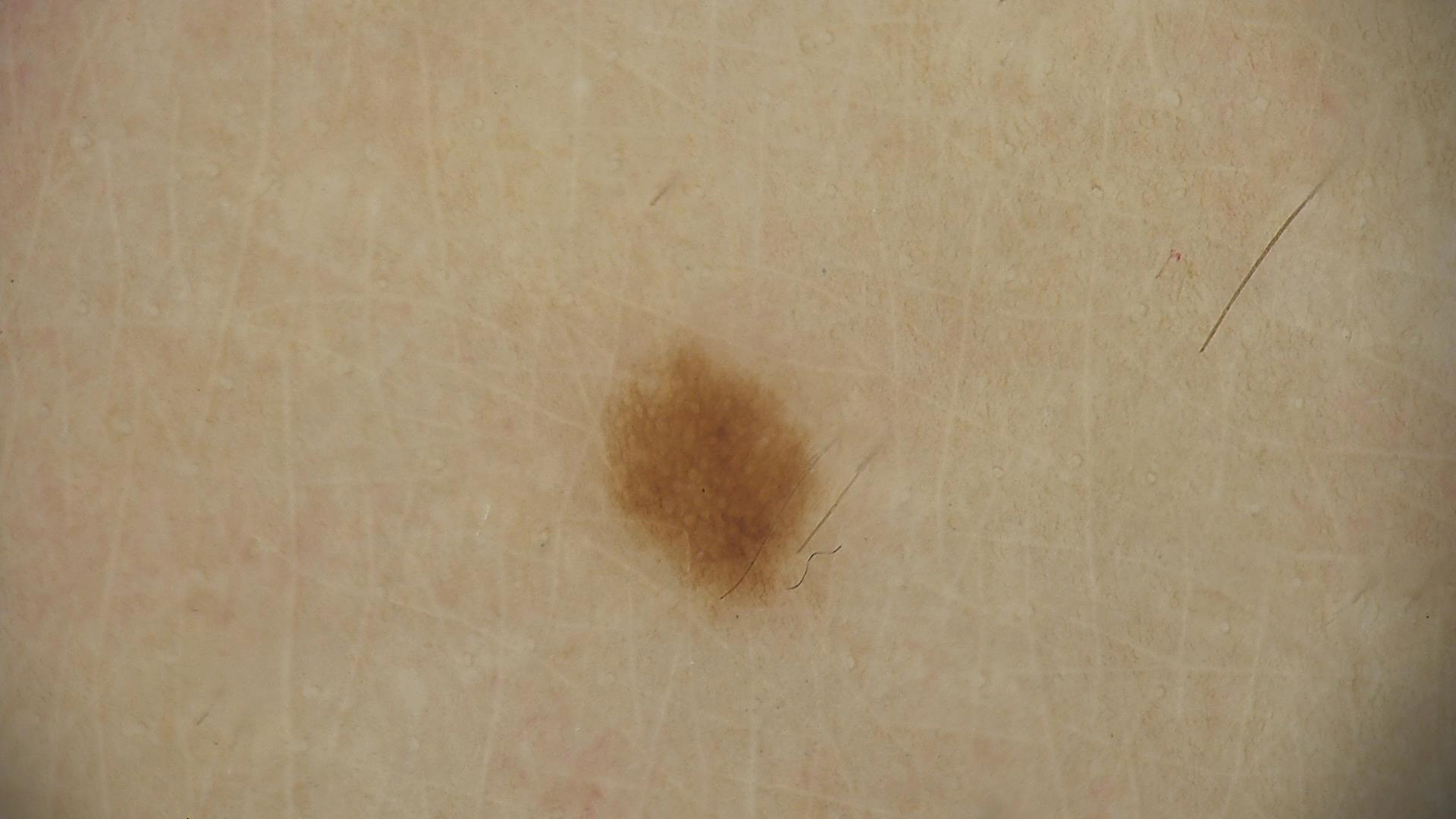| key | value |
|---|---|
| image type | dermoscopy |
| category | banal |
| assessment | junctional nevus (expert consensus) |